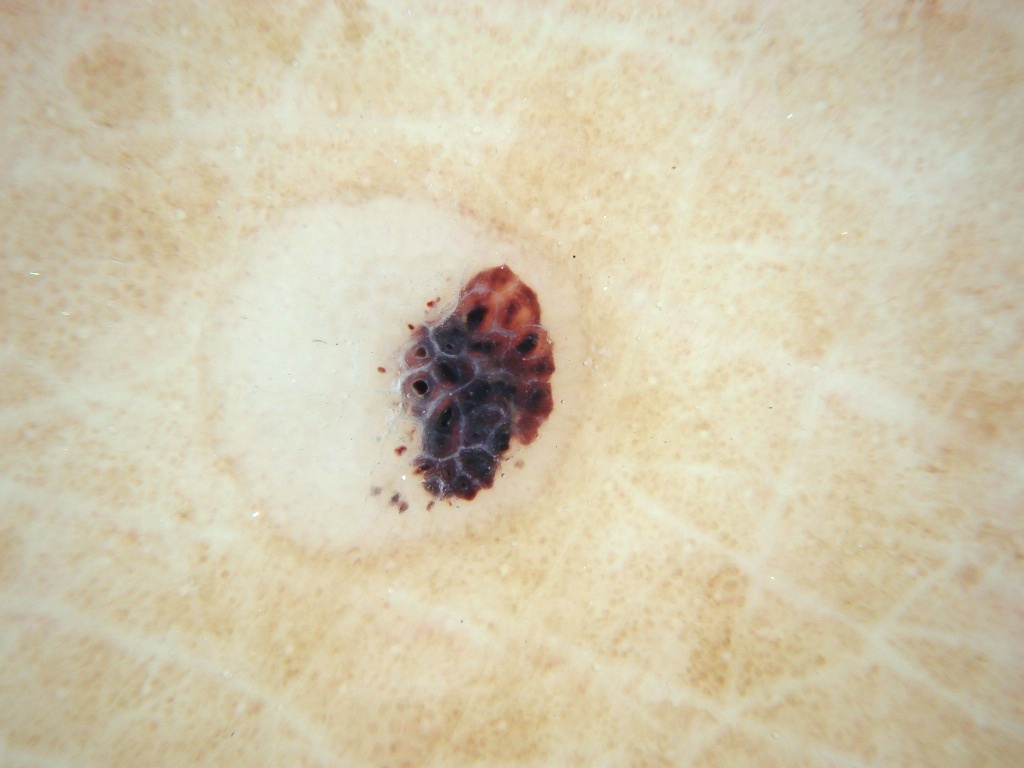A female patient aged 78 to 82. A dermoscopic close-up of a skin lesion. The lesion takes up a moderate portion of the field. Dermoscopy demonstrates no globules, milia-like cysts, streaks, negative network, or pigment network. With coordinates (x1, y1, x2, y2), lesion location: bbox=[186, 188, 591, 571]. The biopsy diagnosis was a melanoma.